Reported lesion symptoms include bothersome appearance and itching. Reported duration is one to four weeks. The lesion involves the head or neck. The patient is female. The contributor notes the lesion is rough or flaky. An image taken at an angle.
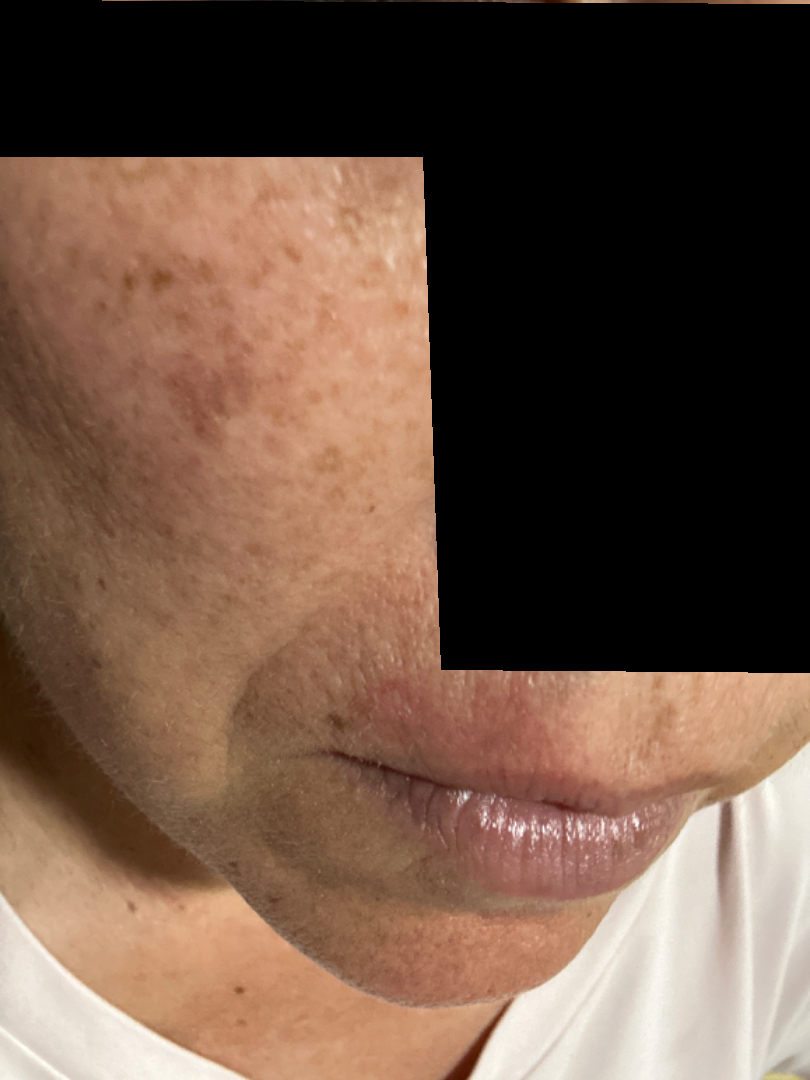Findings: The differential includes Cutaneous lupus, Cutaneous sarcoidosis and Allergic Contact Dermatitis, with no clear leading consideration.